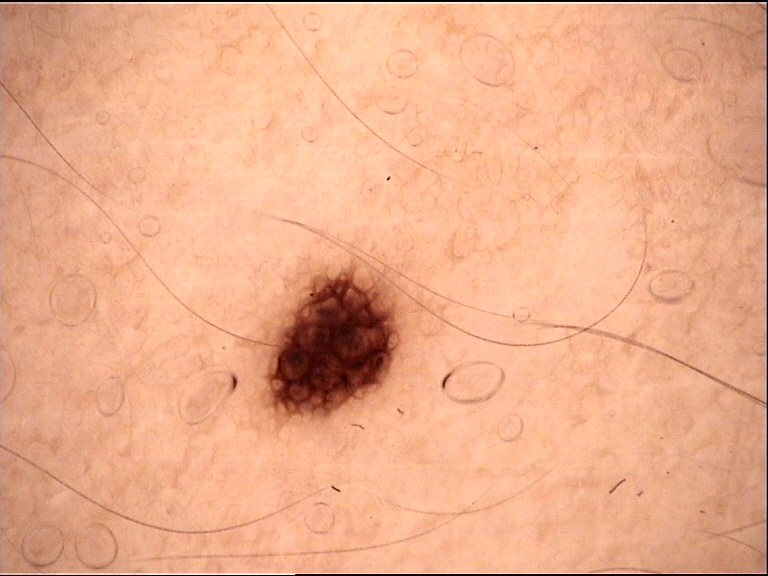image = dermatoscopy, assessment = dysplastic junctional nevus (expert consensus).